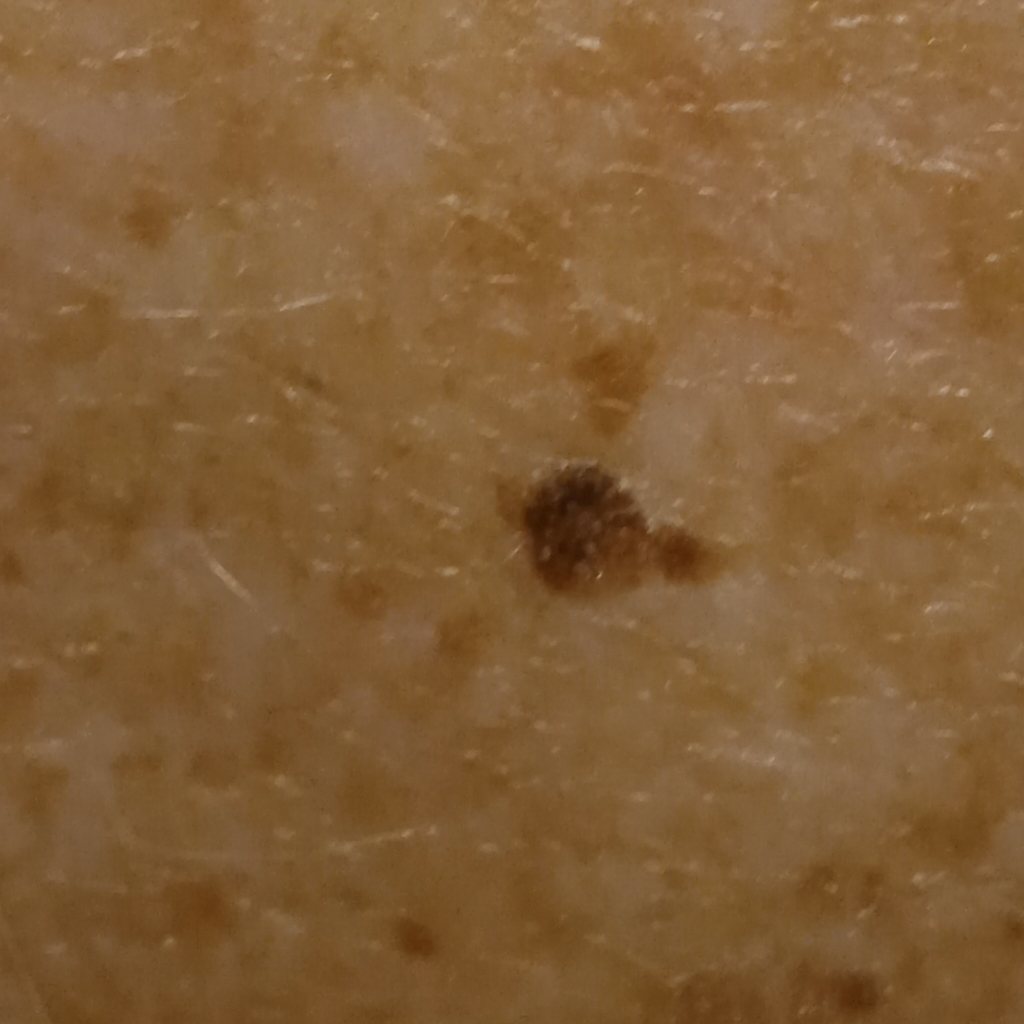Q: What was the diagnosis?
A: seborrheic keratosis (dermatologist consensus)